Reported lesion symptoms include itching · the contributor notes the lesion is raised or bumpy · this image was taken at an angle · the arm is involved · female subject, age 60–69 · the patient considered this a rash:
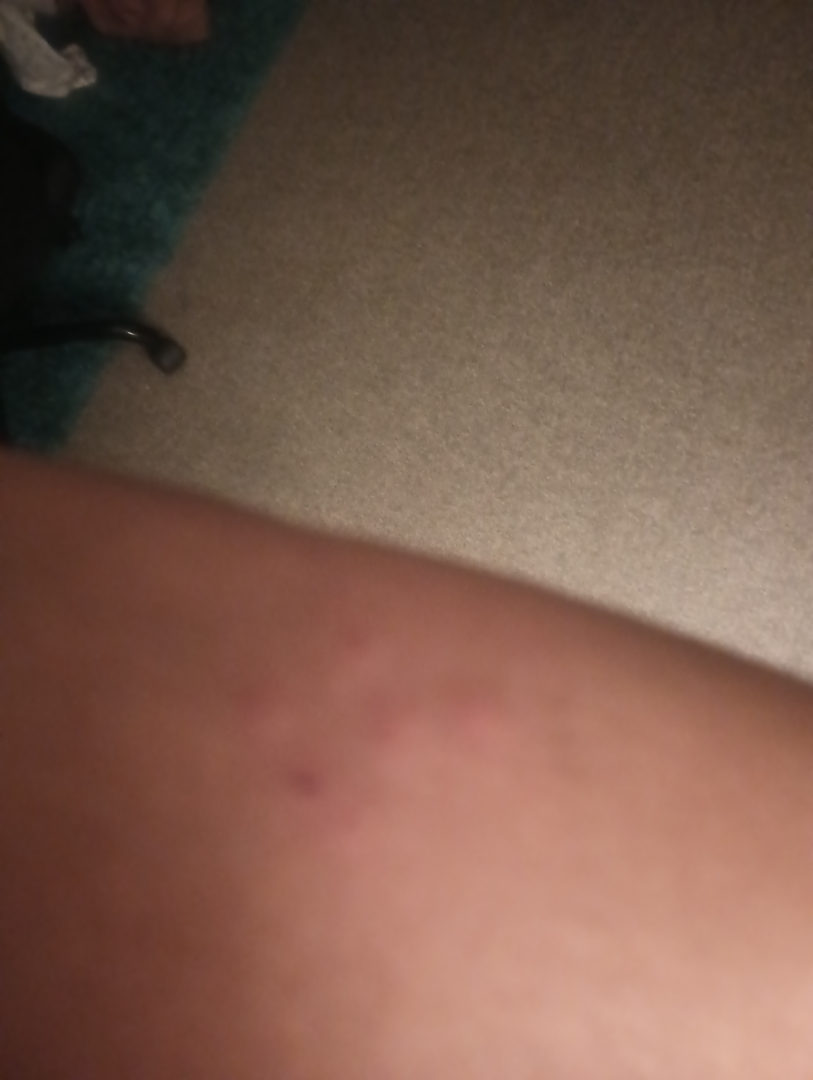Review:
On teledermatology review: the differential is split between Abscess and Hidradenitis.